A close-up photograph, the lesion involves the arm: 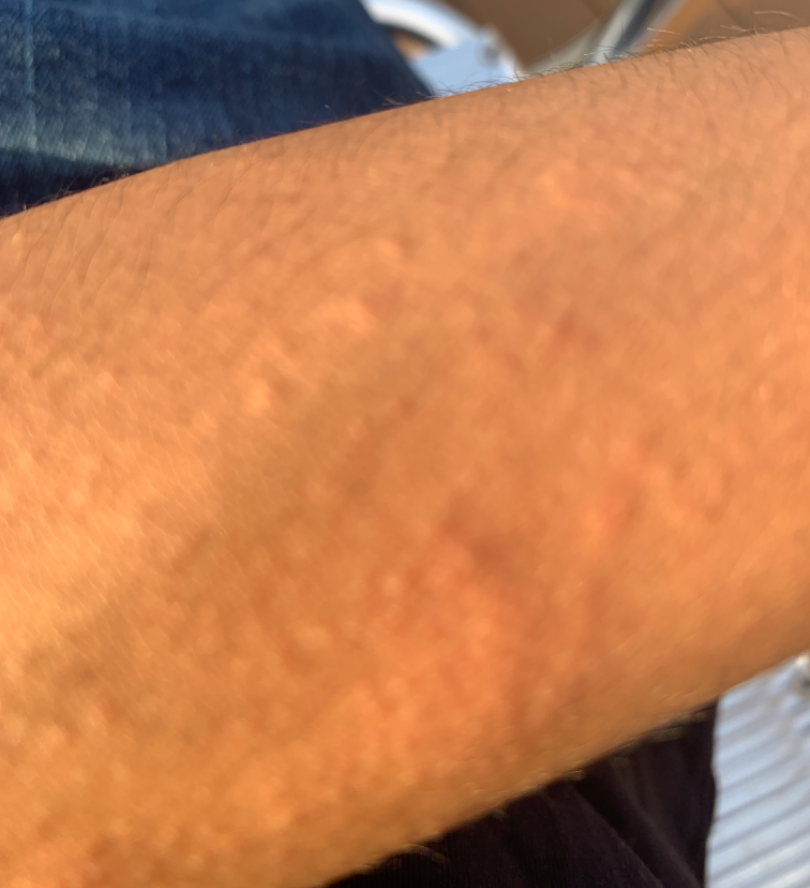The dermatologist could not determine a likely condition from the photograph alone.